The leg, front of the torso and arm are involved. The condition has been present for less than one week. The patient notes bothersome appearance, burning and itching. An image taken at an angle. The patient is 18–29, female. The patient considered this a rash. The lesion is described as raised or bumpy — 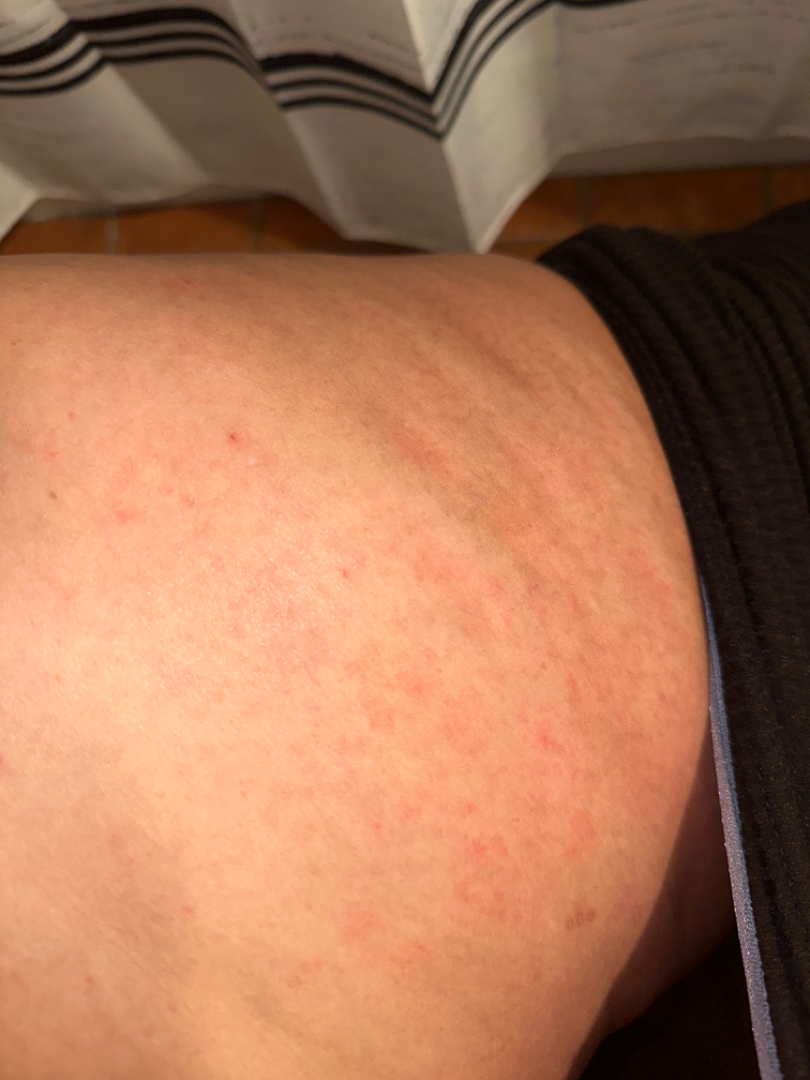| field | value |
|---|---|
| dermatologist impression | Contact dermatitis (primary) |